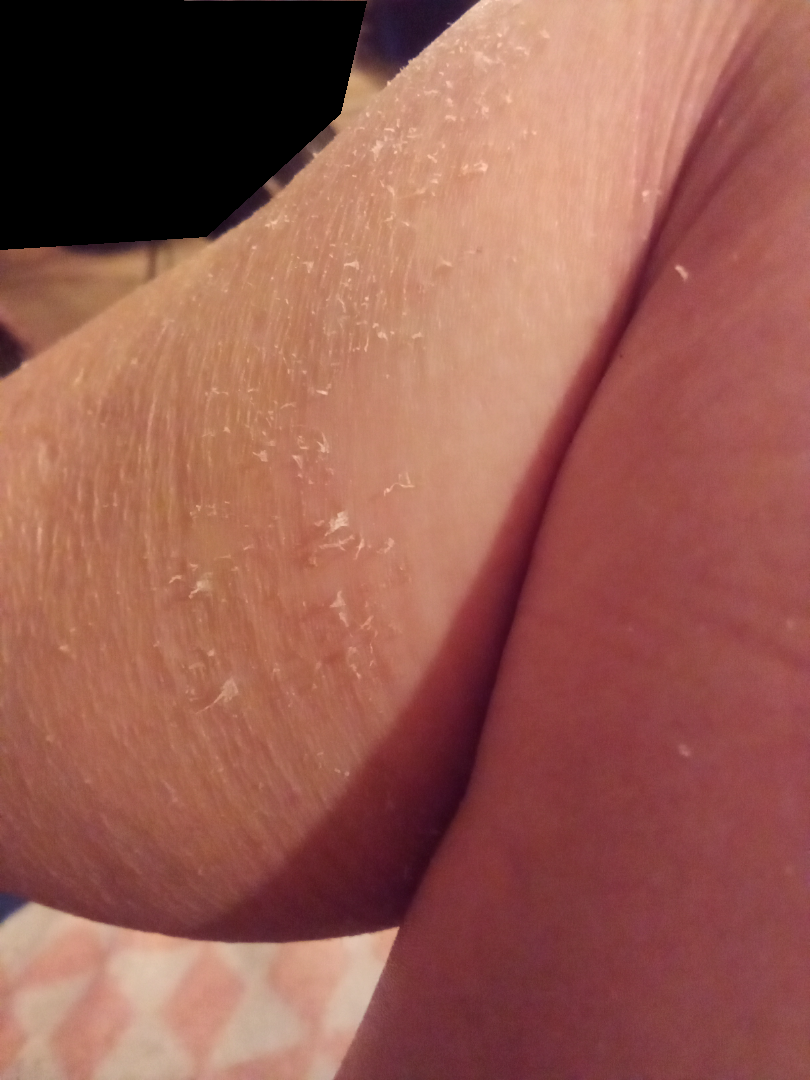• photo taken — close-up
• dermatologist impression — Xerosis, Ichthyosis and Eczema were each considered, in no particular order